The lesion is associated with pain, burning and itching; self-categorized by the patient as a rash; present for more than one year; the palm and back of the hand are involved; the photo was captured at an angle; the patient reports the lesion is raised or bumpy and rough or flaky; the subject is a female aged 18–29: 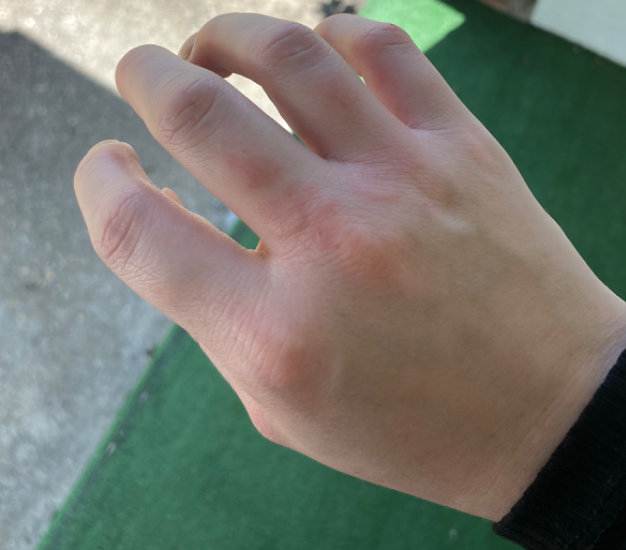differential diagnosis: the primary impression is Granuloma annulare; a more distant consideration is Insect Bite; less probable is Allergic Contact Dermatitis; less likely is Eczema.